Dermoscopy of a skin lesion:
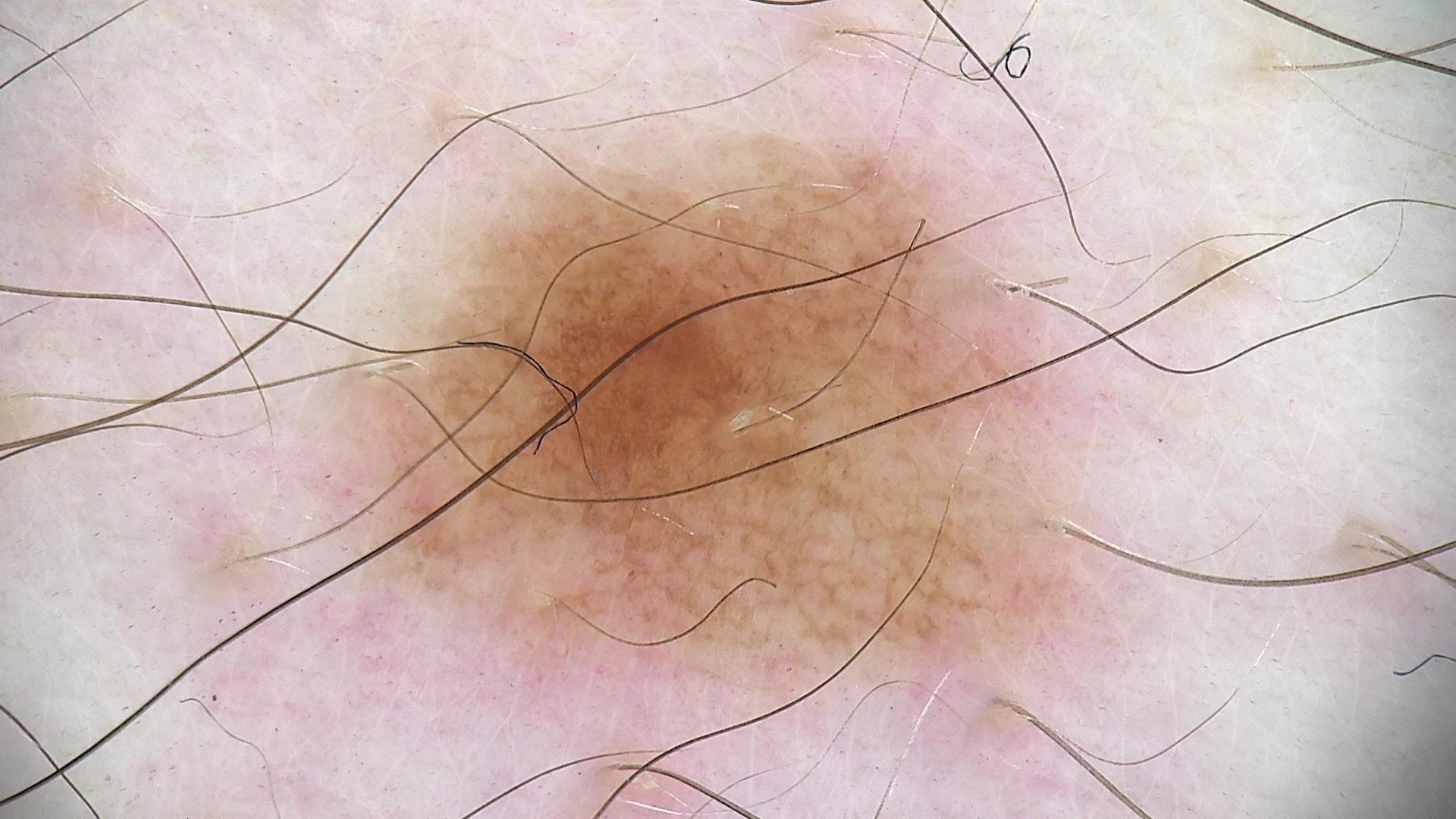diagnosis: compound nevus (expert consensus).